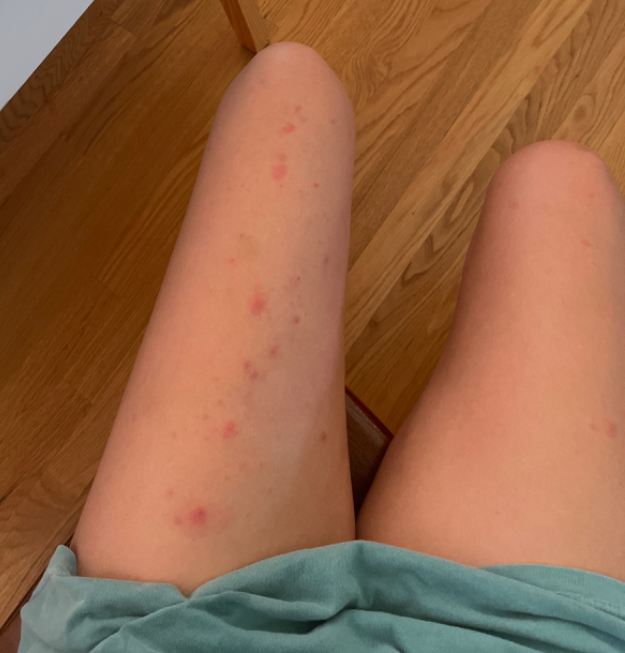Background: The leg is involved. This image was taken at a distance. Findings: On remote dermatologist review: in keeping with Folliculitis.